The patient describes having few moles overall · a macroscopic clinical photograph of a skin lesion · acquired for a research image collection, with no referral diagnosis · the patient says their skin reddens with sun exposure · a male subject aged 62.
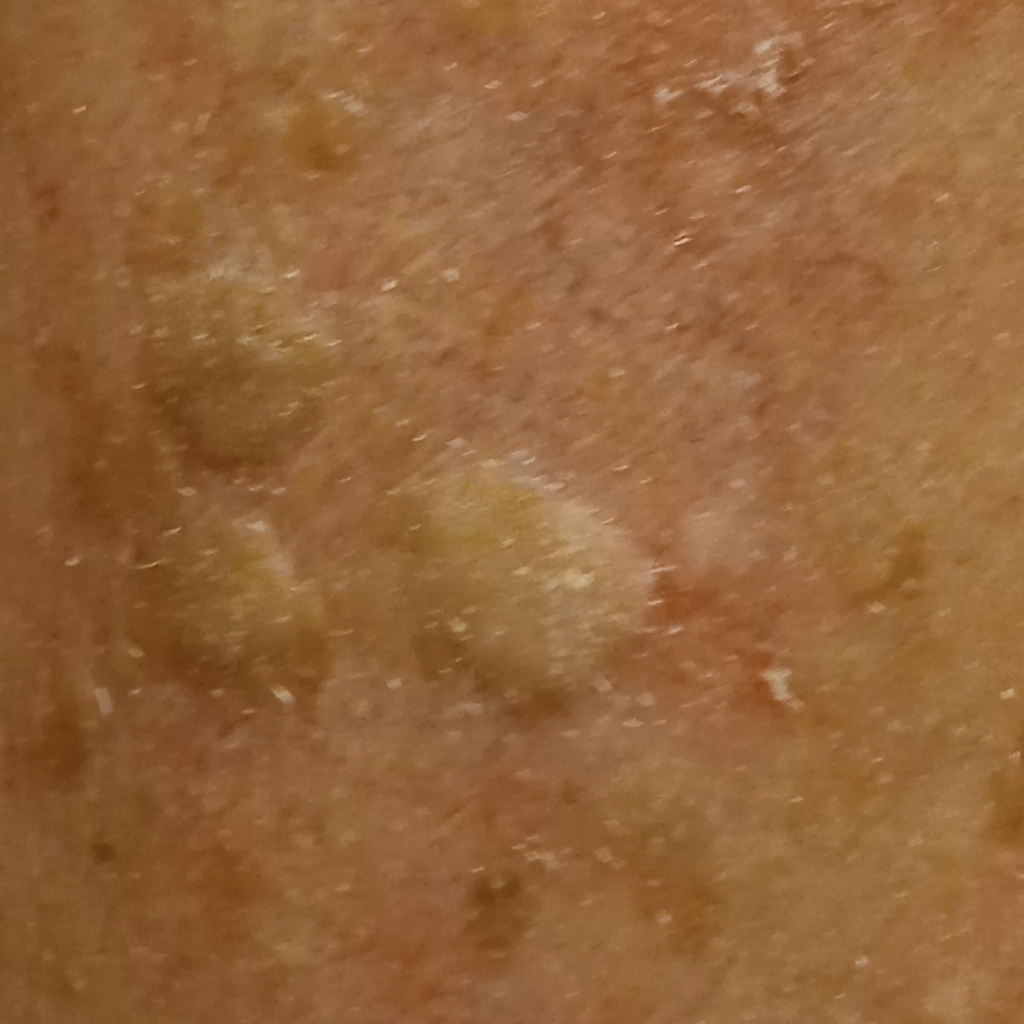- location: the face
- size: 7.5 mm
- diagnosis: seborrheic keratosis (dermatologist consensus)